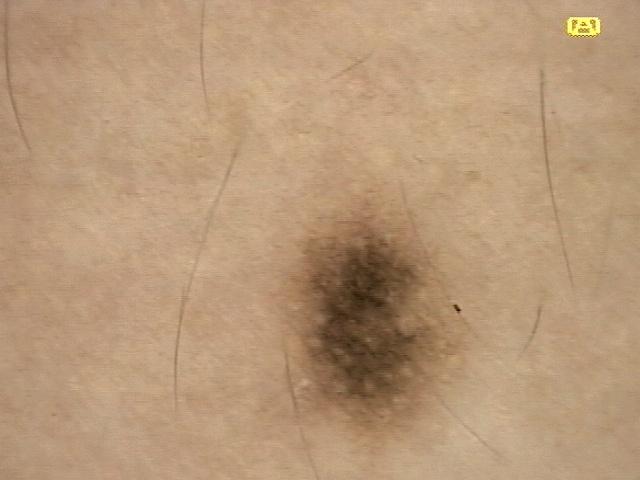A female subject about 30 years old.
Recorded as Fitzpatrick II.
A skin lesion imaged with contact-polarized dermoscopy.
The lesion involves the trunk.
The clinical assessment was a lesion of melanocytic lineage — a nevus.